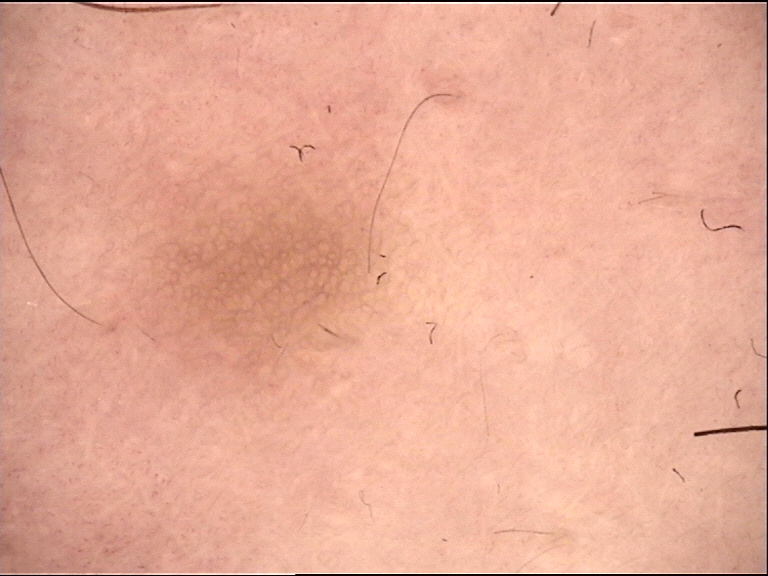Summary:
A dermoscopic close-up of a skin lesion.
Impression:
The diagnosis was a dermatofibroma.